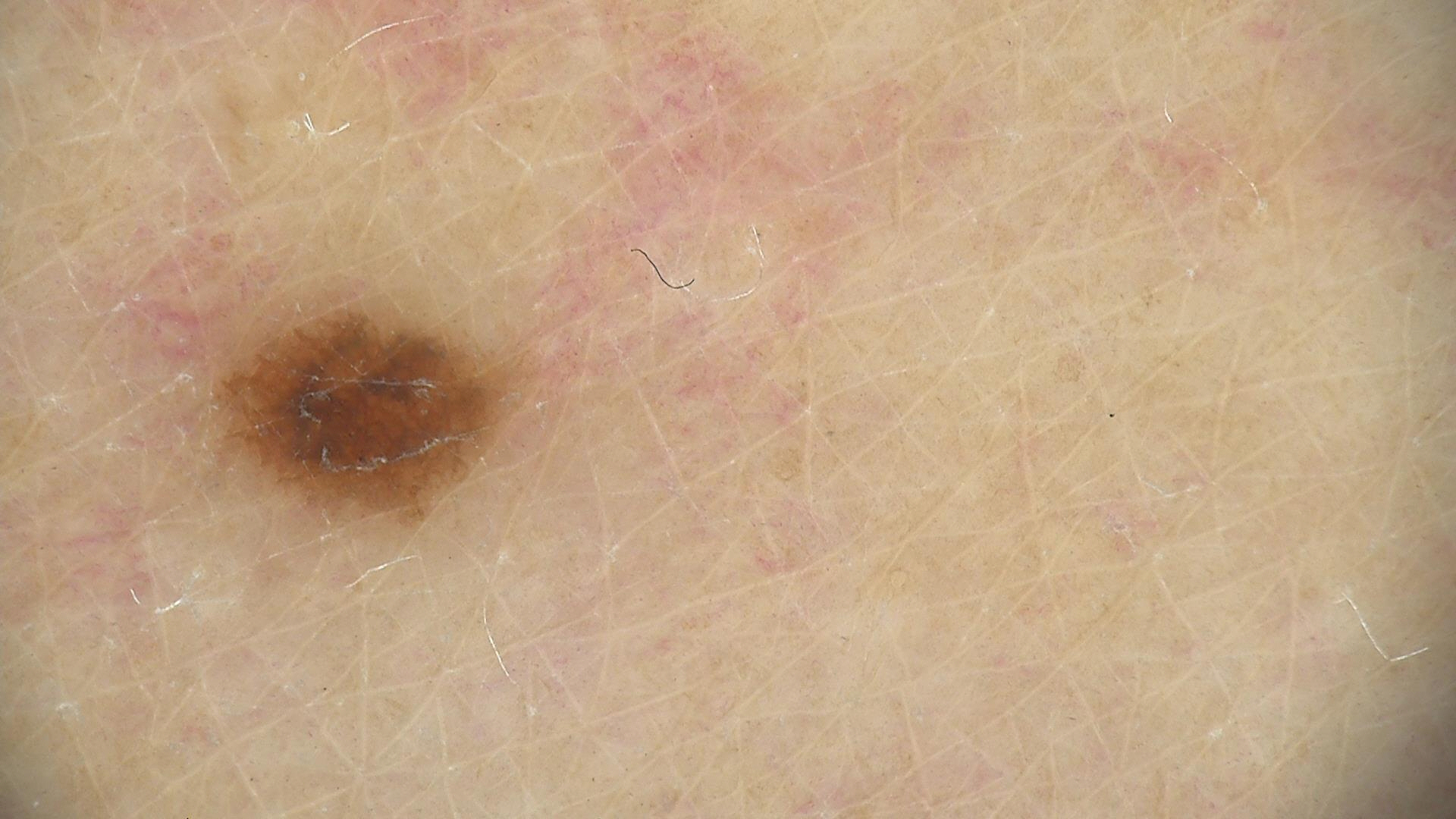A dermoscopic image of a skin lesion.
Classified as a dysplastic junctional nevus.